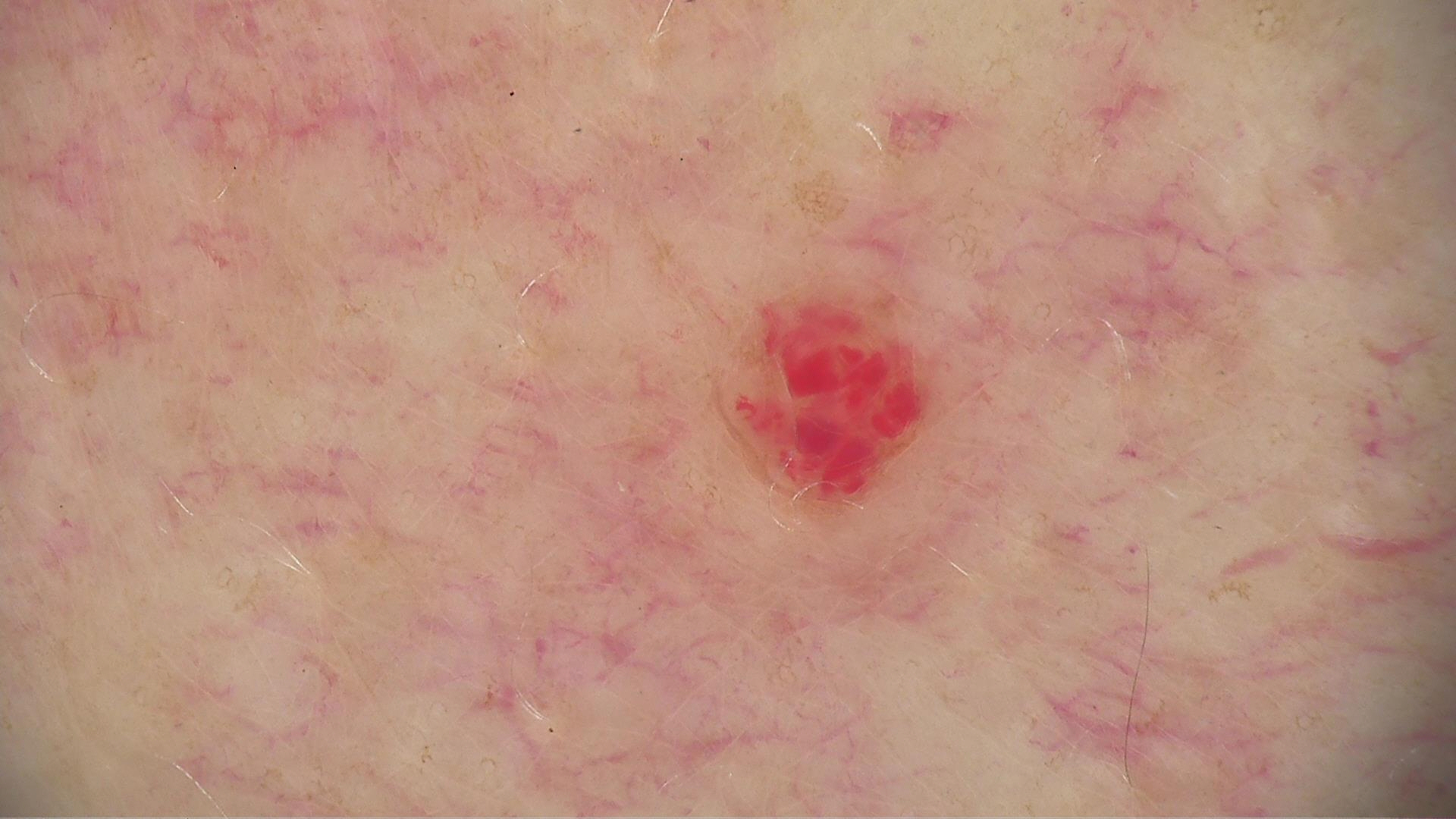The diagnostic label was a hemangioma.